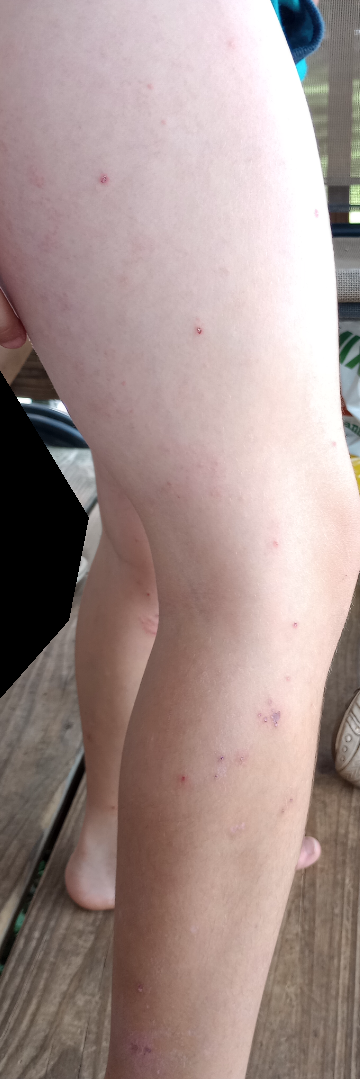assessment: indeterminate | image framing: at a distance | symptom duration: less than one week | self-categorized as: a rash | texture: raised or bumpy | anatomic site: back of the torso, front of the torso, leg, back of the hand and arm | constitutional symptoms: none reported.